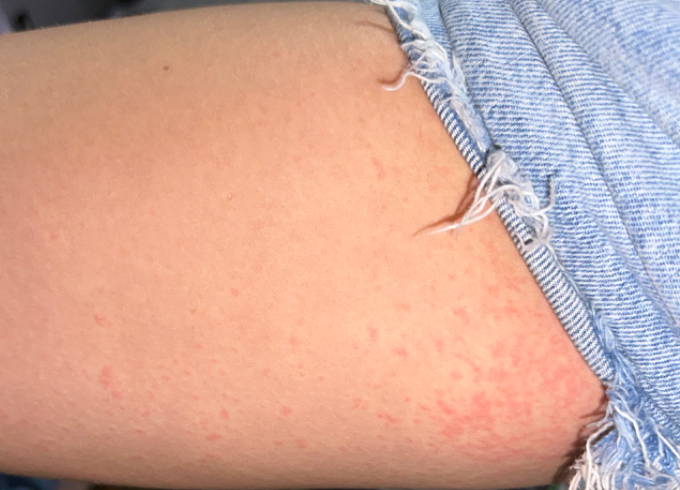<dermatology_case>
<assessment>unable to determine</assessment>
<systemic_symptoms>none reported</systemic_symptoms>
<texture>flat</texture>
<shot_type>at an angle</shot_type>
<body_site>back of the torso, leg</body_site>
<duration>about one day</duration>
<patient>female, age 18–29</patient>
<patient_category>a rash</patient_category>
</dermatology_case>